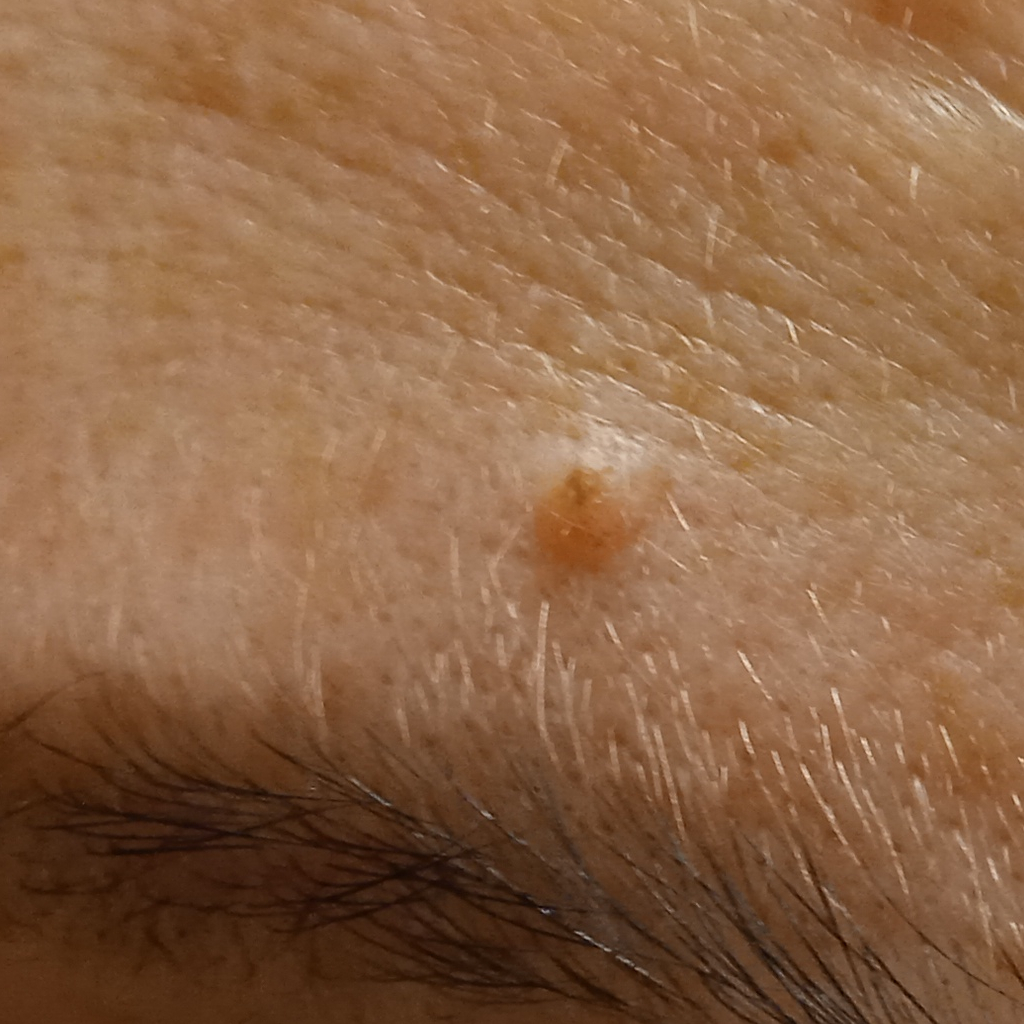A clinical photograph of a skin lesion.
A female subject 50 years of age.
The patient says their skin reddens painfully with sun exposure.
Referred with a clinical suspicion of melanoma.
A moderate number of moles by the patient's own estimate.
The lesion is on the face.
The lesion measures approximately 1.8 mm.
Dermatologist review favored a melanocytic nevus.